The patient says their skin tans without first burning. By self-report, a history of sunbed use. Acquired for a research image collection, with no referral diagnosis. A clinical close-up of a skin lesion. A female patient 47 years old. The patient describes having a moderate number of moles:
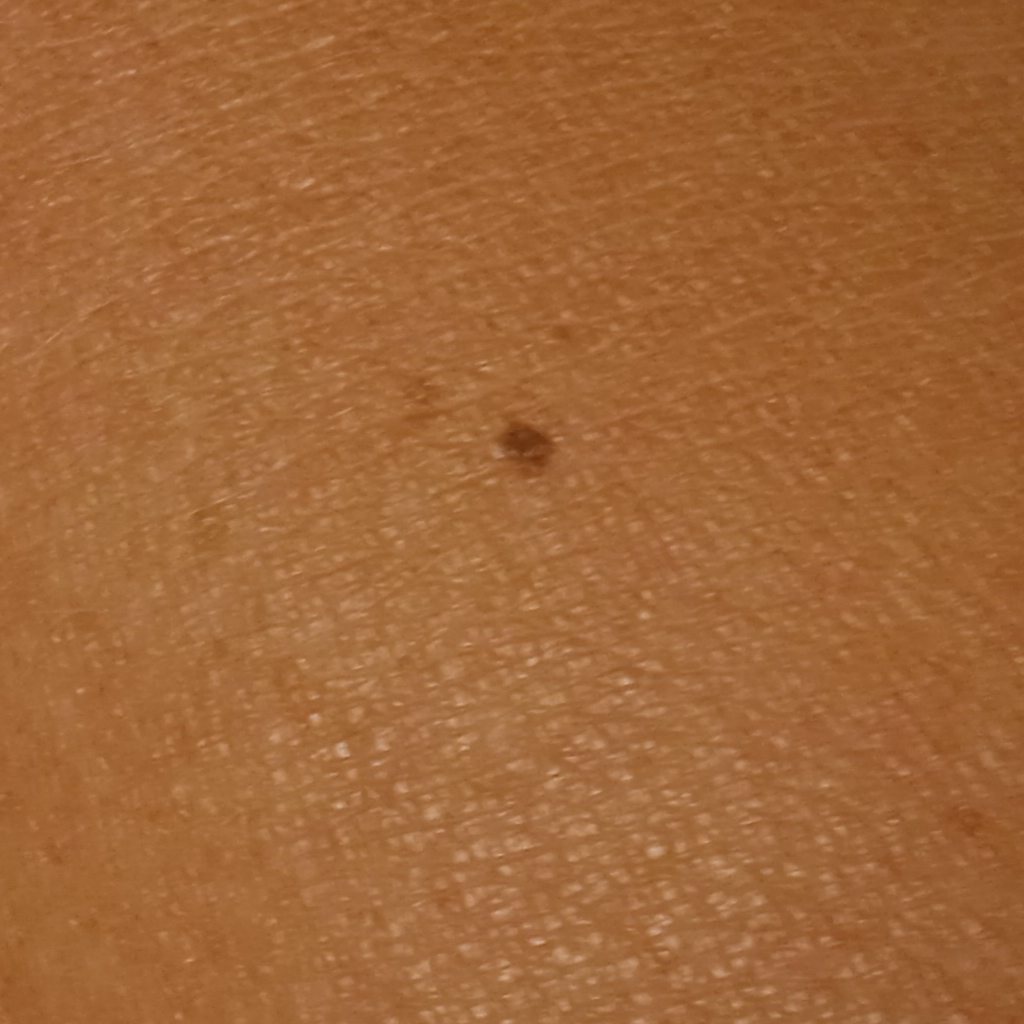Summary:
The lesion measures approximately 1.8 mm.
Conclusion:
The consensus diagnosis for this lesion was a melanocytic nevus.